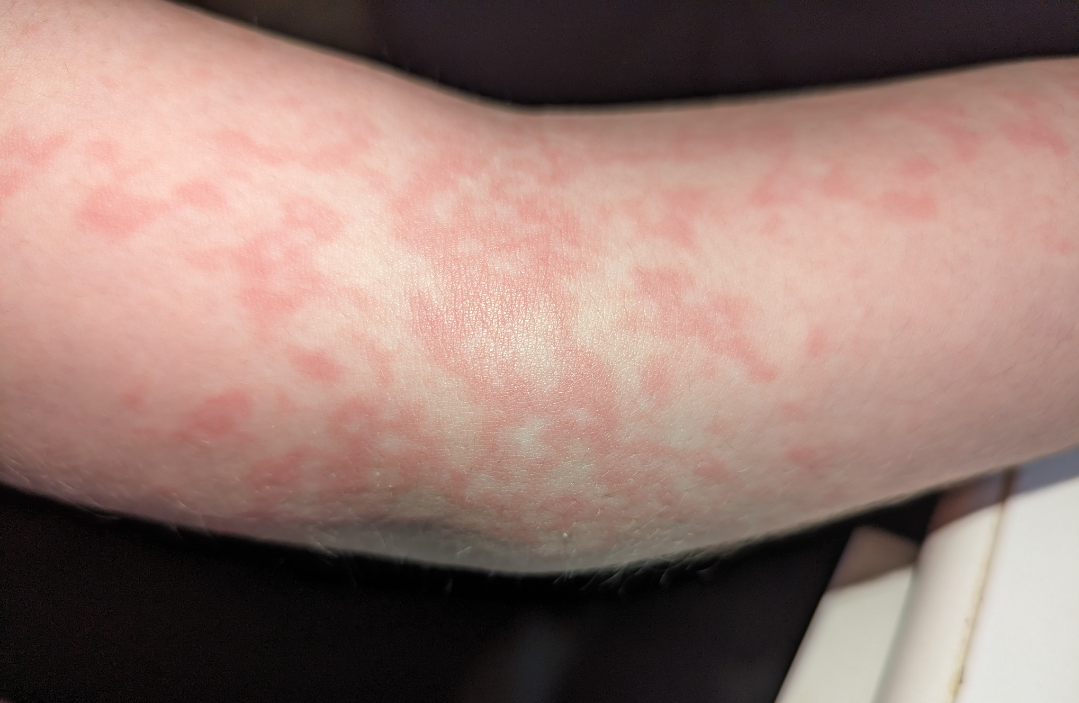Impression:
The reviewer was unable to grade this case for skin condition.
History:
Symptoms reported: bothersome appearance. The patient described the issue as a rash. Female contributor, age 18–29. Texture is reported as flat. The affected area is the arm. This is a close-up image. No relevant systemic symptoms. The patient indicates the condition has been present for less than one week.